The patient indicates the condition has been present for one to four weeks. Reported lesion symptoms include bothersome appearance. The patient described the issue as a rash. The back of the hand, leg and top or side of the foot are involved. The photo was captured at a distance. No associated systemic symptoms reported. The contributor is 60–69, female. The lesion is described as raised or bumpy and rough or flaky. Skin tone: Fitzpatrick phototype I; lay reviewers estimated a Monk Skin Tone of 2 — 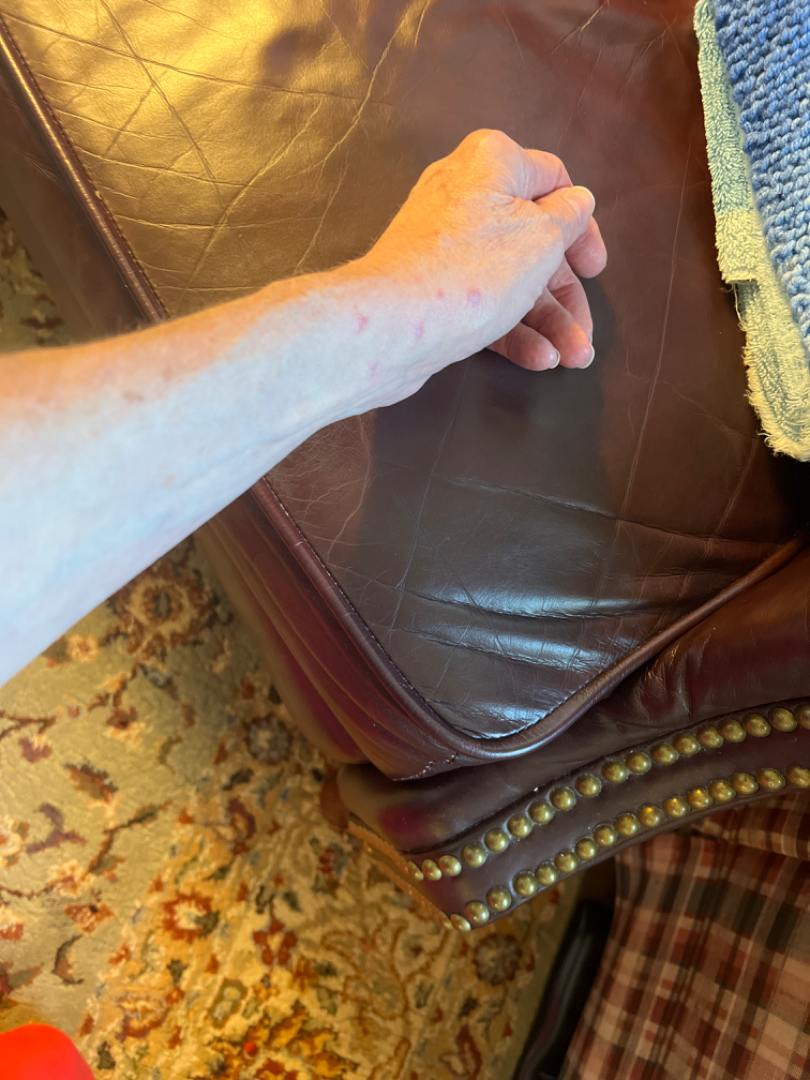On remote review of the image: most likely Impetigo; also on the differential is Skin infection; also consider Lichen planus/lichenoid eruption.